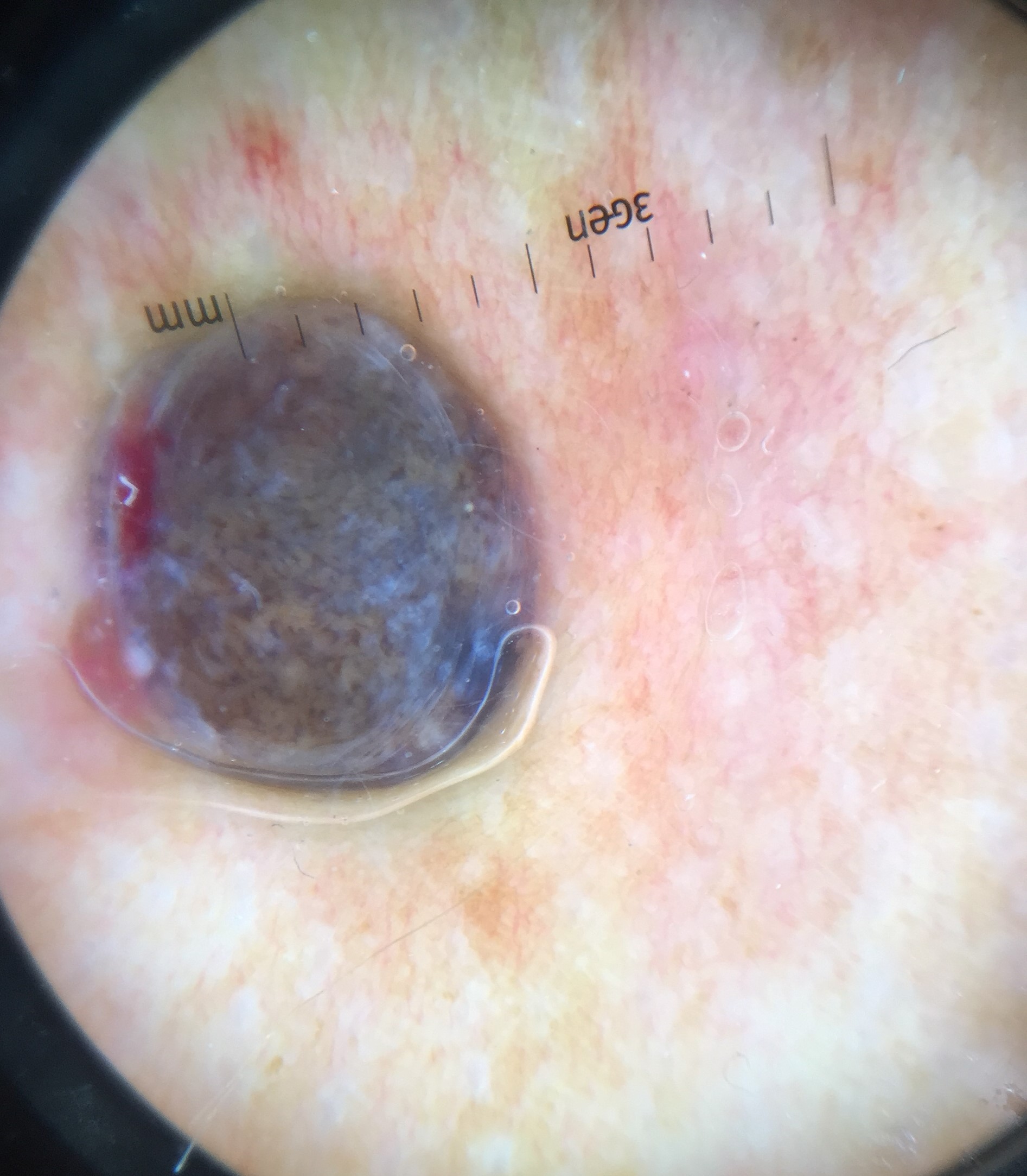* image type: dermatoscopy
* label: melanoma (biopsy-proven)